This image was taken at an angle; the patient notes the lesion is raised or bumpy; the lesion is associated with itching; the lesion involves the leg; the contributor is 60–69, female; the condition has been present for one to three months; no associated systemic symptoms reported: 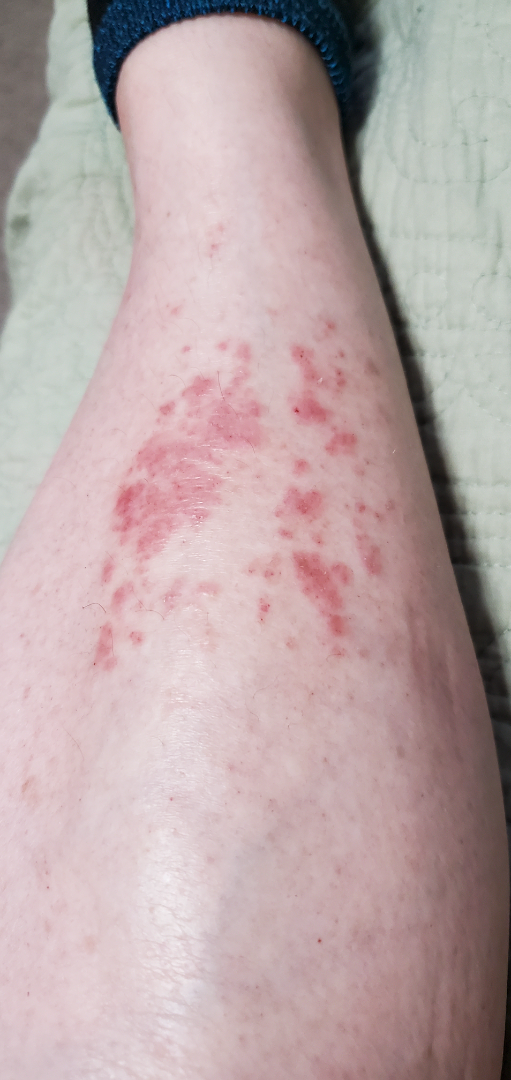| field | value |
|---|---|
| diagnostic considerations | most likely Allergic Contact Dermatitis; also consider Eczema; possibly Pigmented purpuric eruption |